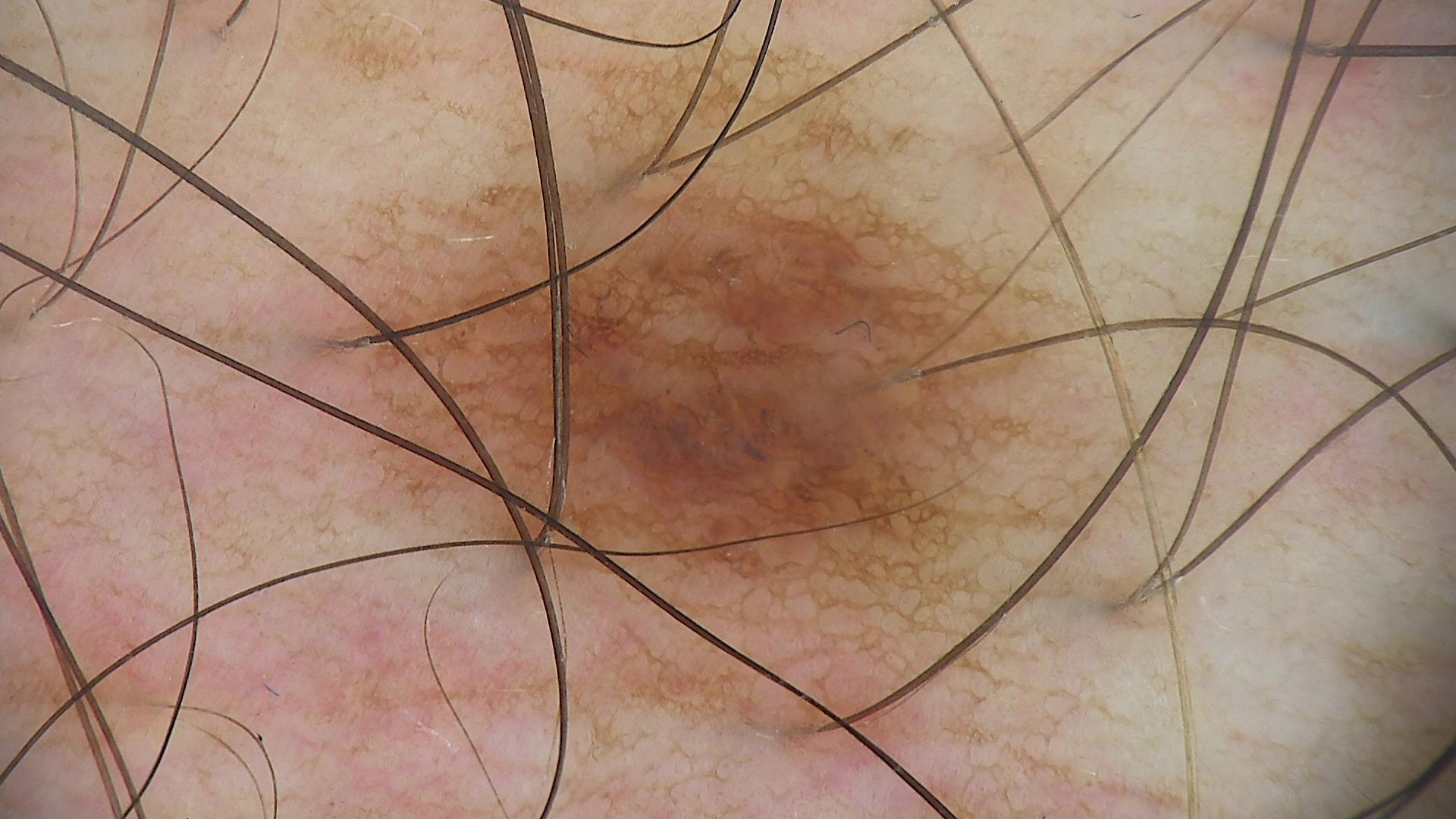The diagnosis was a benign lesion — a dysplastic junctional nevus.